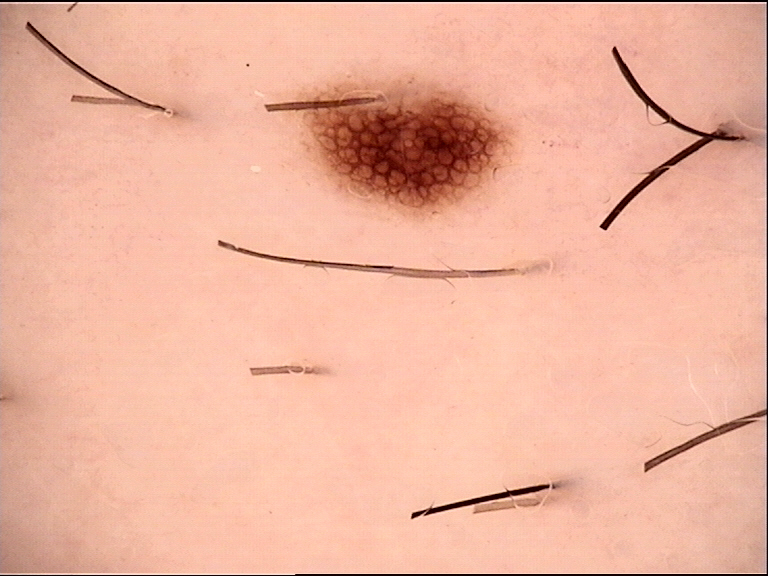Case:
• image type · dermatoscopy
• assessment · dysplastic junctional nevus (expert consensus)